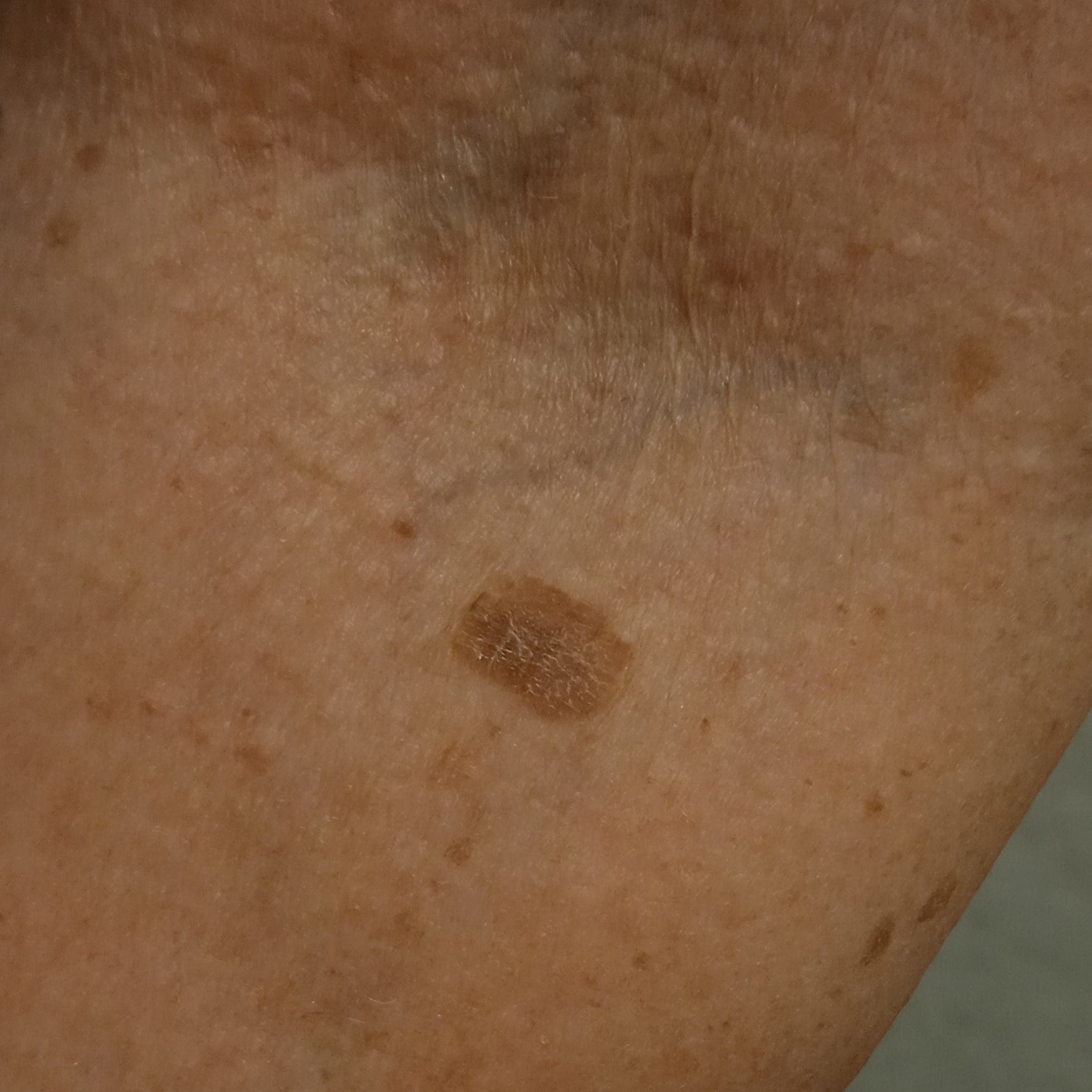A female patient 84 years of age. A clinical close-up of a skin lesion. Collected as part of a research study, without a referral diagnosis. The lesion is on an arm. Measuring roughly 11.2 mm. The dermatologists' assessment was a seborrheic keratosis.